A dermoscopy image of a skin lesion · by self-report, a family history of skin cancer and a history of sunbed use · the patient says their skin reddens painfully with sun exposure · few moles overall by the patient's own estimate · a female patient age 48 · acquired for a research image collection, with no referral diagnosis:
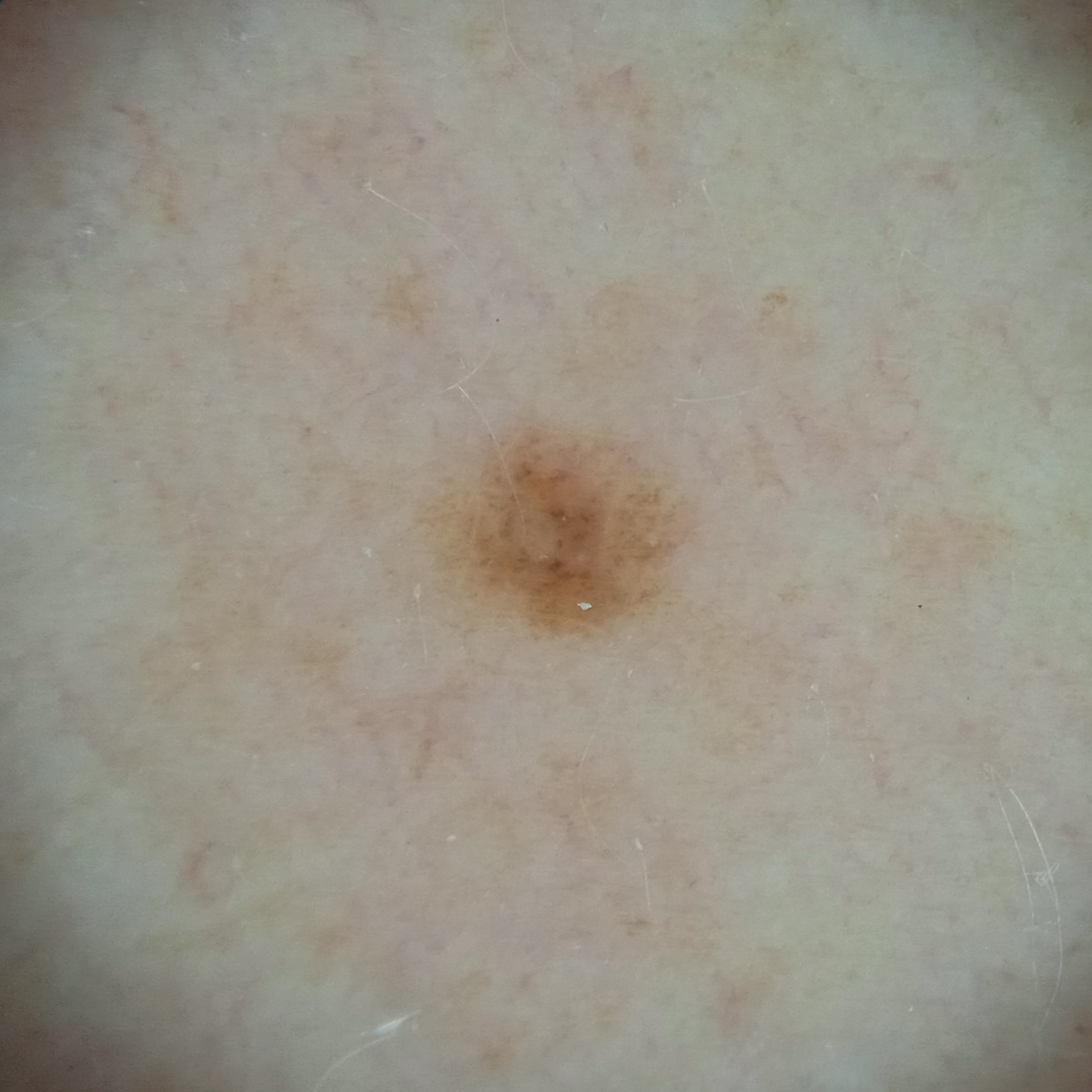– lesion size · 2.7 mm
– diagnosis · melanocytic nevus (dermatologist consensus)